A male subject aged around 80. Contact-polarized dermoscopy of a skin lesion. Skin type II.
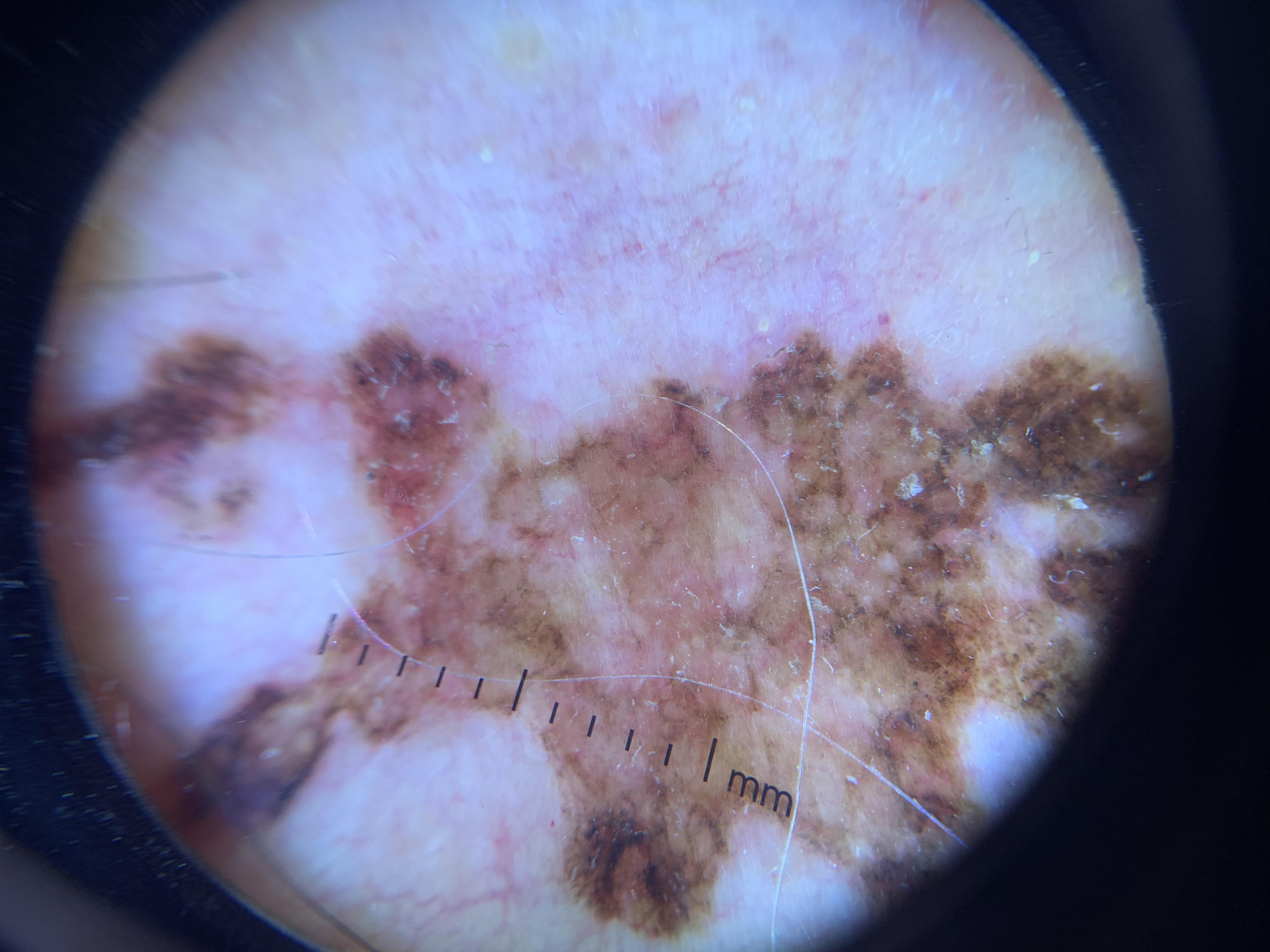Notes:
– site · the anterior trunk
– diagnosis · Melanoma (biopsy-proven)